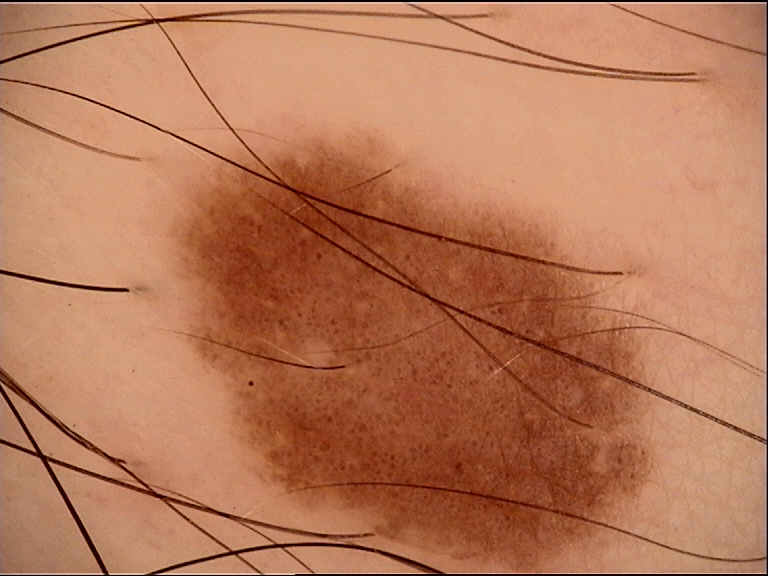A skin lesion imaged with a dermatoscope. The diagnosis was a benign lesion — a dysplastic junctional nevus.